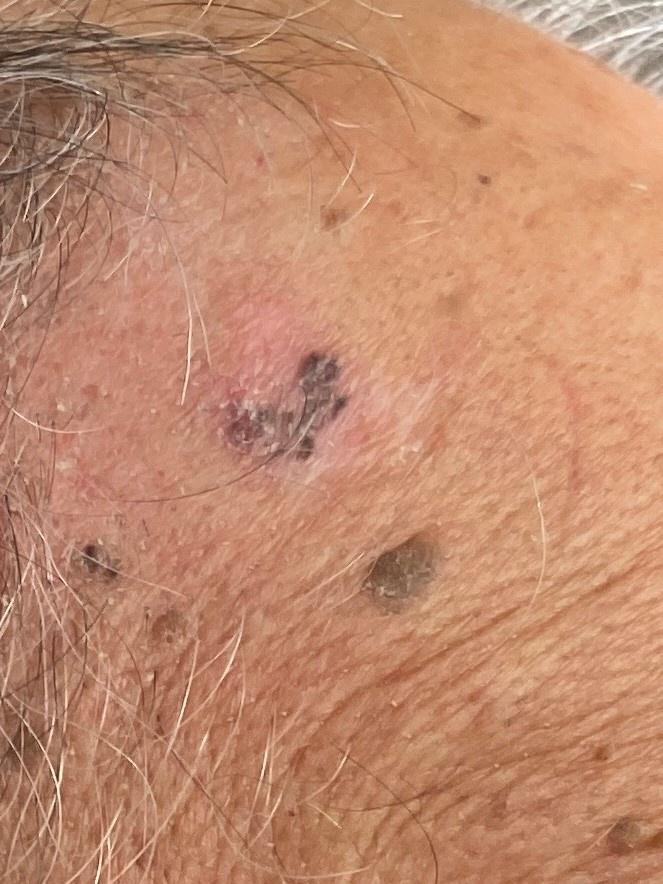Findings:
– image type: clinical photo (overview)
– subject: male, roughly 85 years of age or older
– anatomic site: the head or neck
– pathology: Basal cell carcinoma (biopsy-proven)